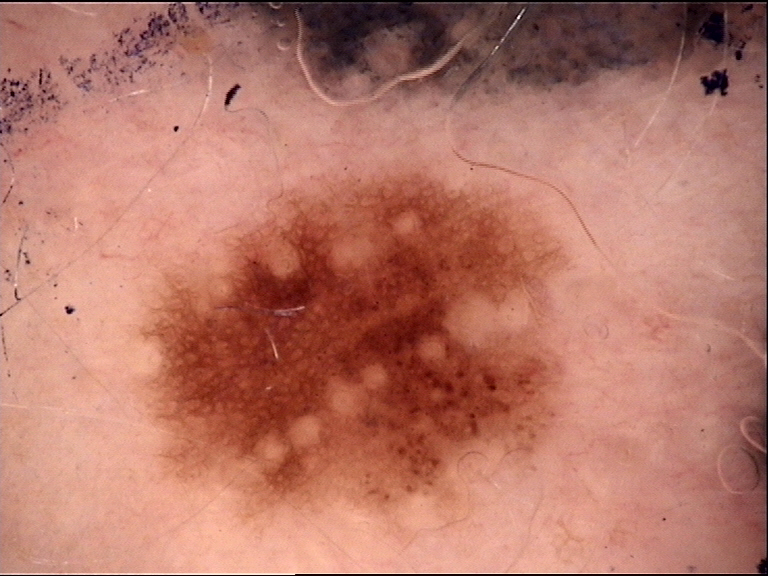A skin lesion imaged with a dermatoscope. The diagnostic label was a dysplastic junctional nevus.